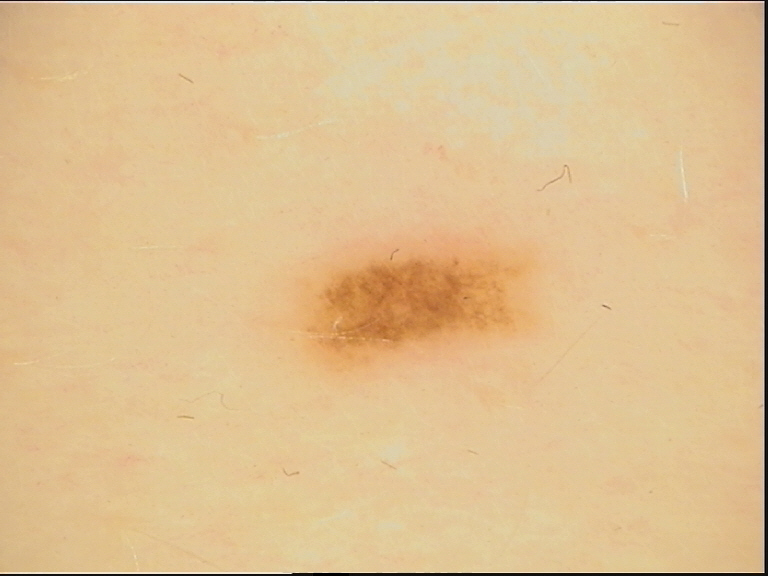Summary:
A dermoscopic photograph of a skin lesion.
Conclusion:
Diagnosed as a benign lesion — a dysplastic junctional nevus.